An image taken at an angle. The lesion involves the leg — 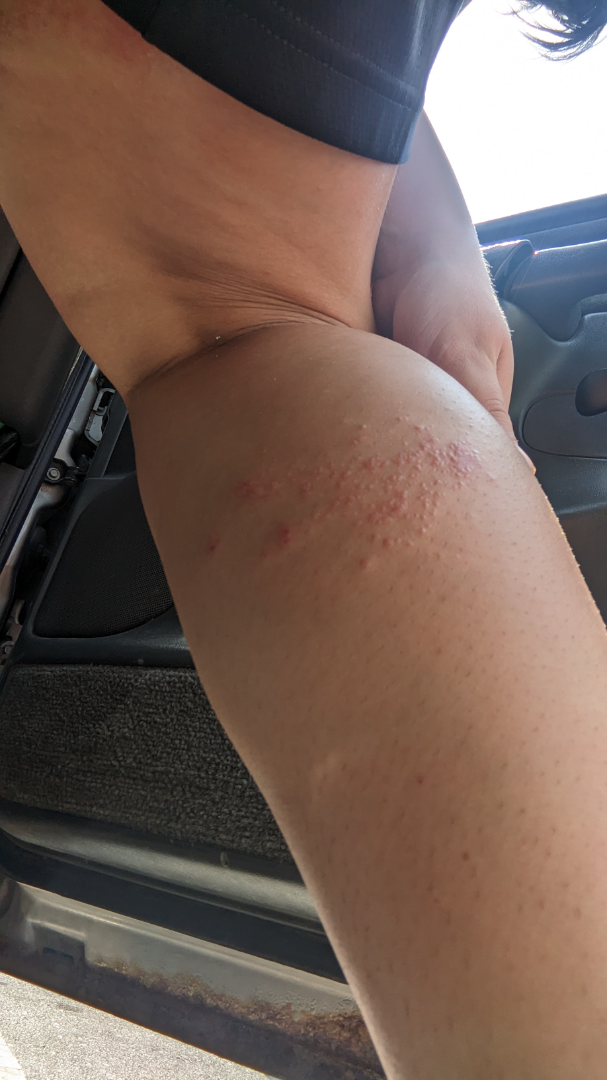{
  "assessment": "ungradable on photographic review",
  "texture": [
    "raised or bumpy",
    "rough or flaky"
  ],
  "duration": "one to four weeks"
}